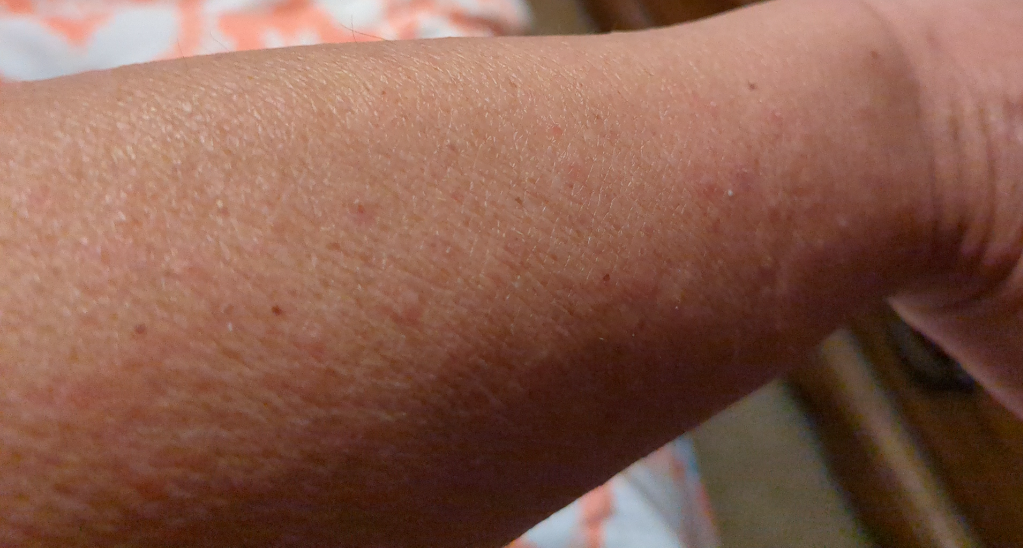The patient also reports chills and fatigue.
FST III; lay graders estimated MST 3–4.
Close-up view.
The lesion involves the arm and back of the hand.
The patient considered this a rash.
The patient reports the lesion is rough or flaky and raised or bumpy.
The patient reports the condition has been present for one to four weeks.
The patient reports bothersome appearance and itching.
On dermatologist assessment of the image: the leading impression is Folliculitis; the differential also includes Eczema.